A clinical close-up photograph of a skin lesion · a subject age 61: 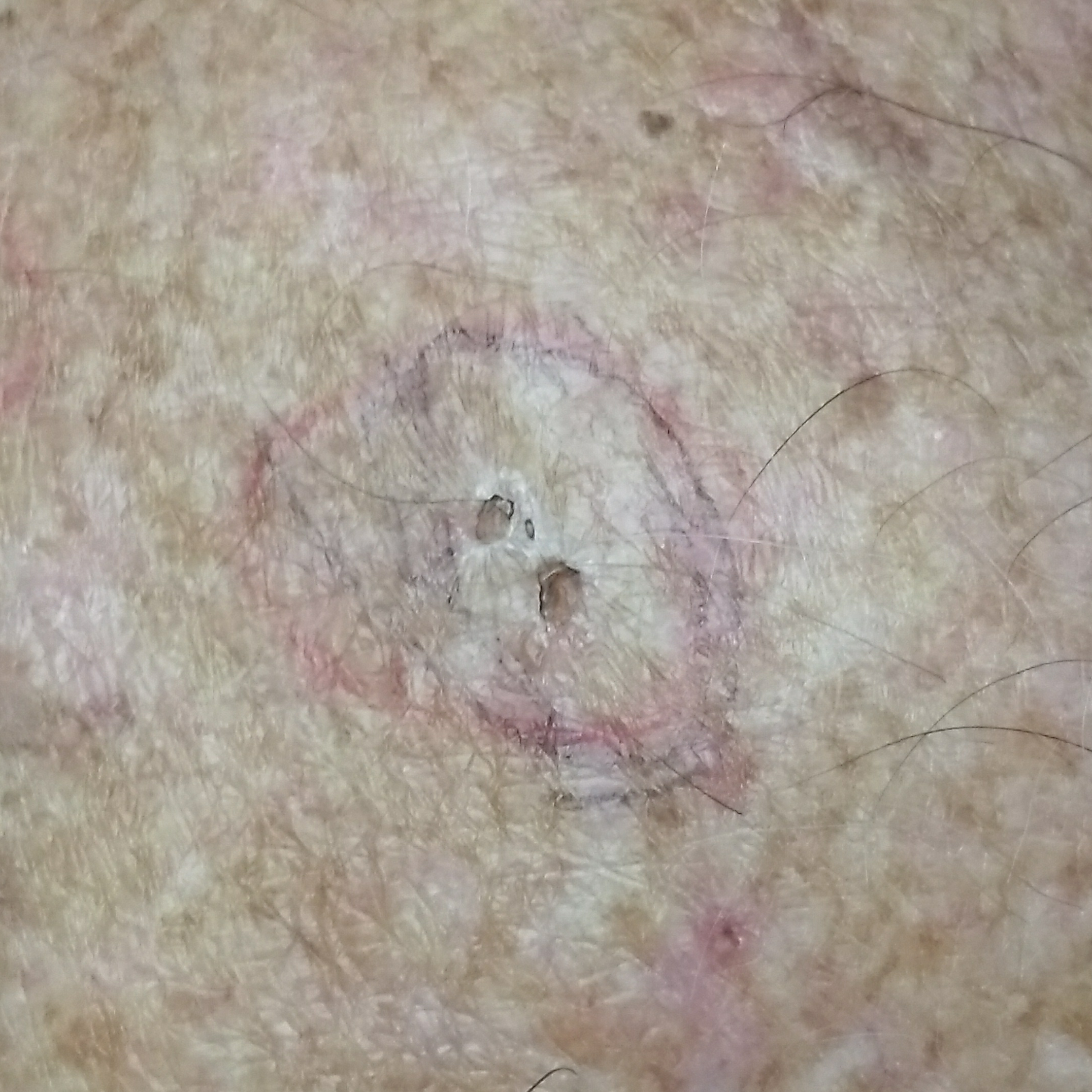The lesion involves the chest. The patient reports that the lesion itches, but does not hurt and is not elevated. Consistent with an actinic keratosis.